Skin tone: Fitzpatrick I; non-clinician graders estimated Monk Skin Tone 2 or 3 (two reviewer pools) · the lesion is described as raised or bumpy and rough or flaky · the head or neck is involved · close-up view.
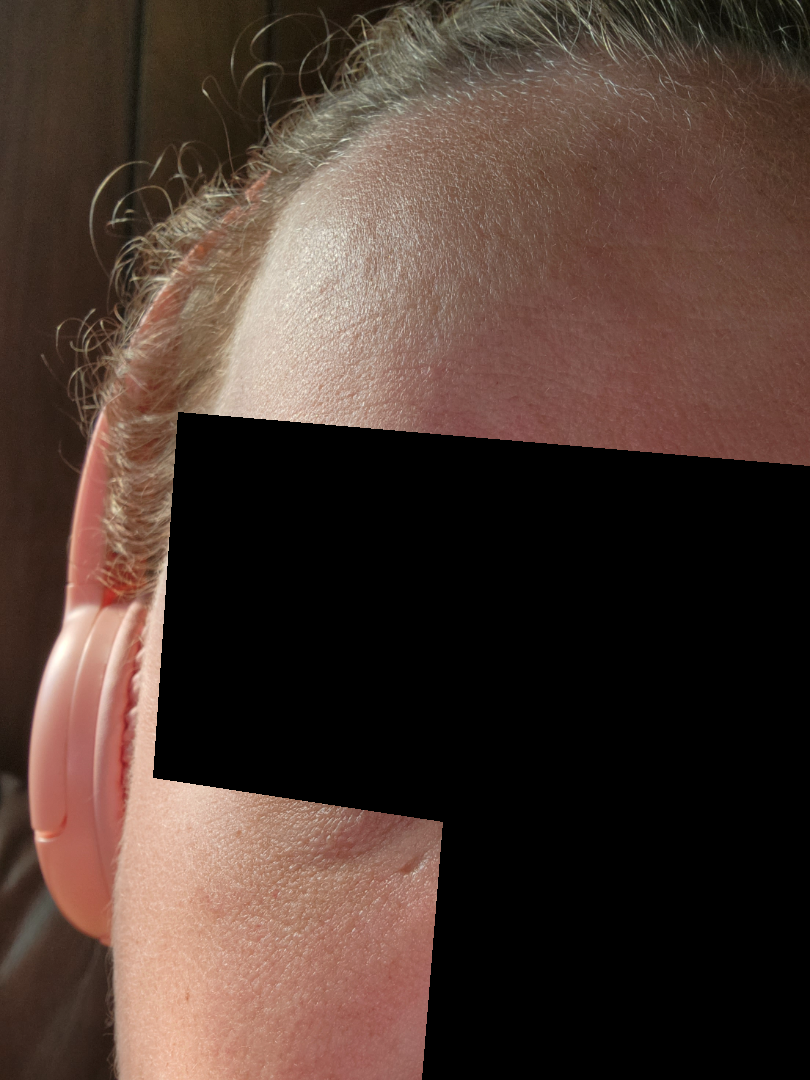The case was indeterminate on photographic review.